The affected area is the leg. This is a close-up image. The contributor is 70–79, female — 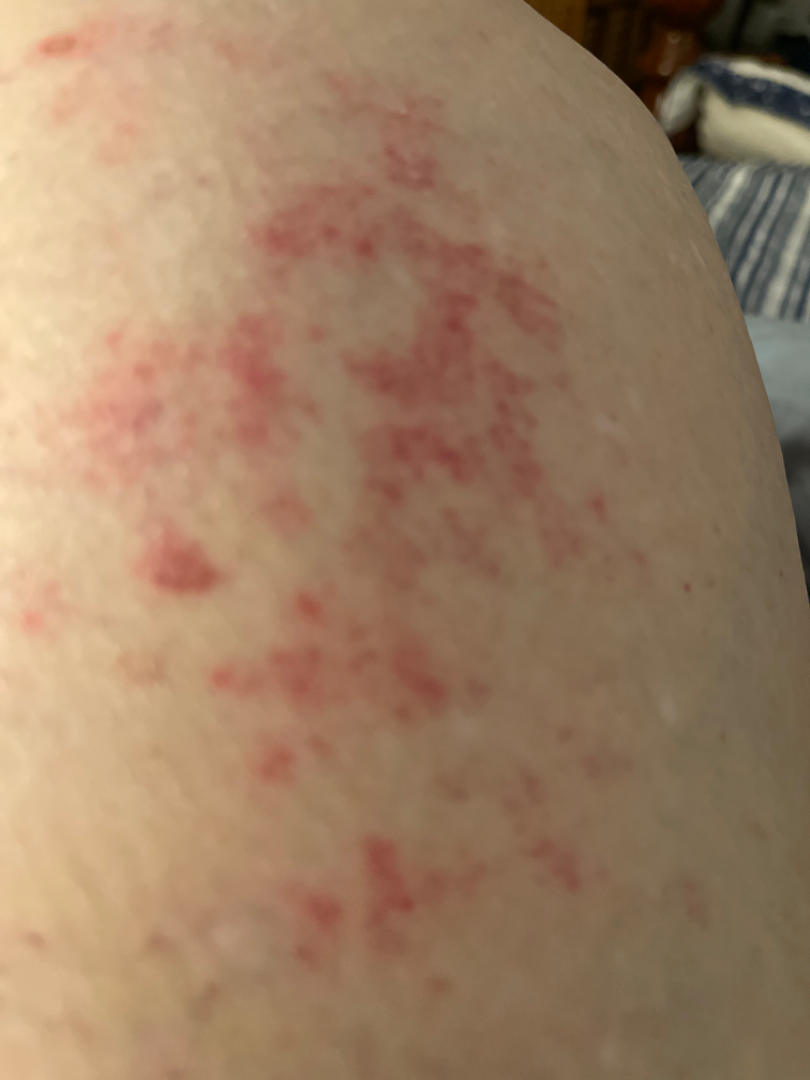No differential diagnosis could be assigned on photographic review.